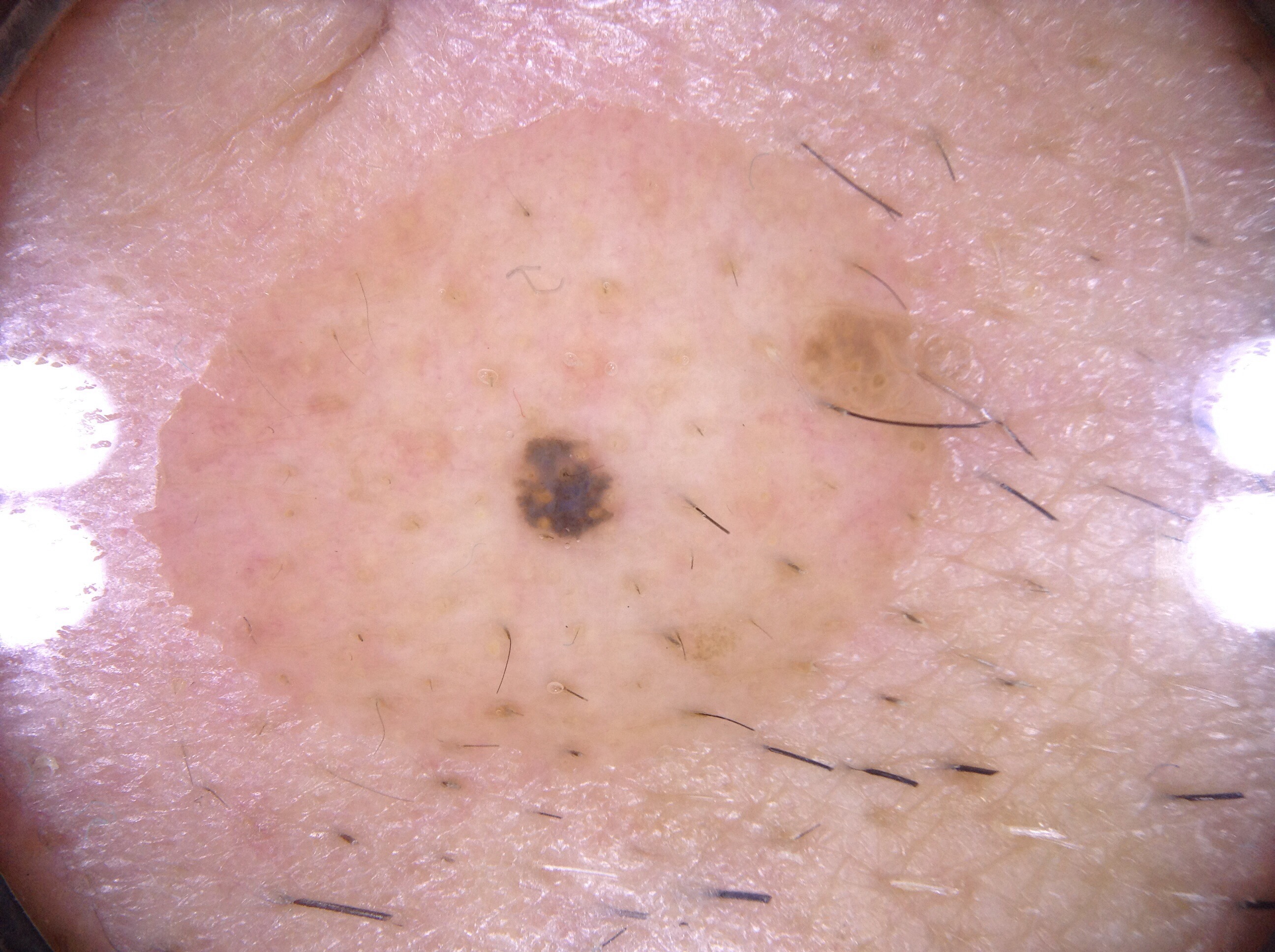<dermoscopy>
<image>
  <modality>dermoscopy</modality>
</image>
<lesion_location>
  <bbox_xyxy>506, 428, 627, 553</bbox_xyxy>
</lesion_location>
<diagnosis>
  <name>seborrheic keratosis</name>
  <malignancy>benign</malignancy>
  <lineage>keratinocytic</lineage>
  <provenance>clinical</provenance>
</diagnosis>
</dermoscopy>